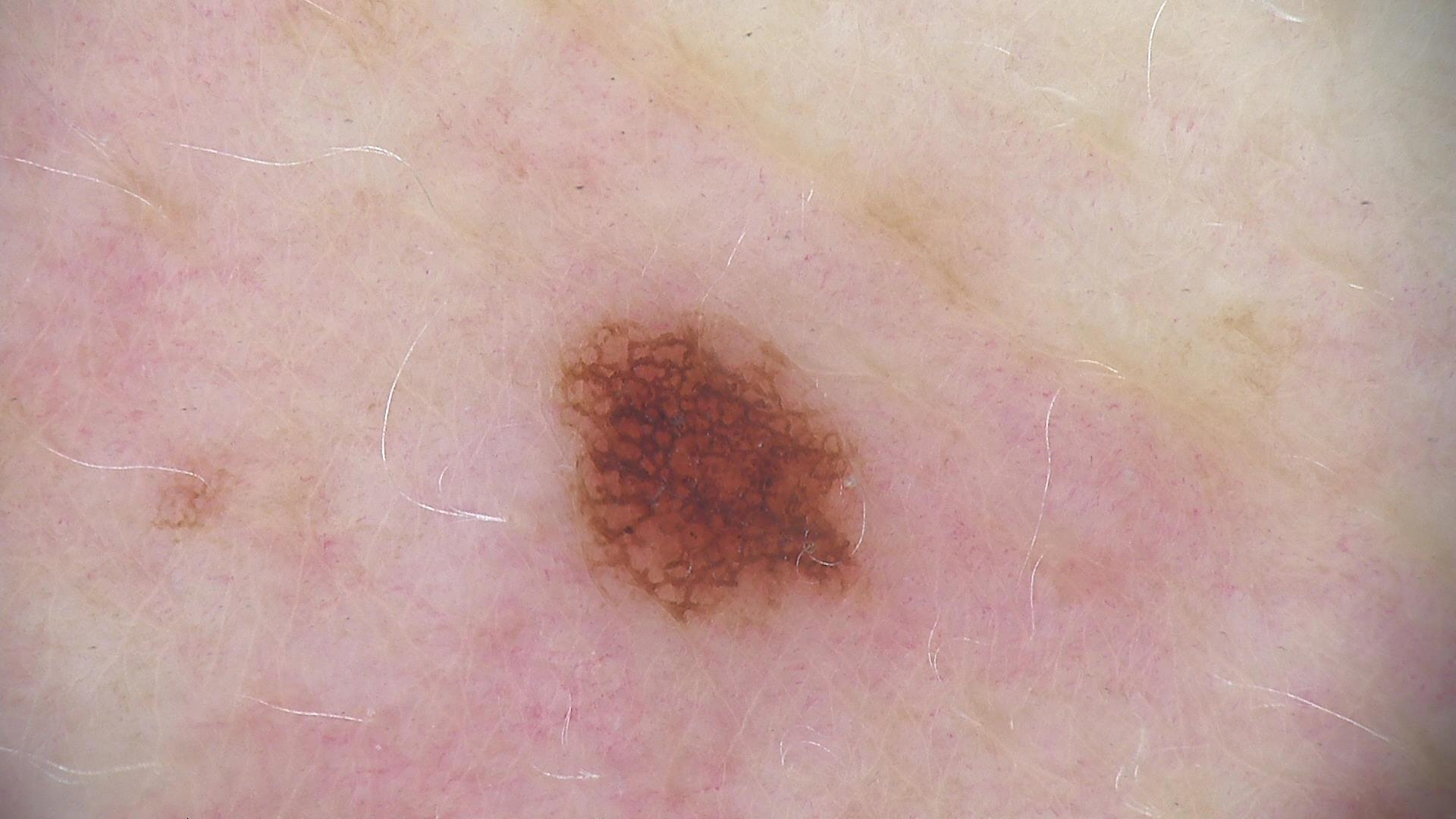| feature | finding |
|---|---|
| image | dermatoscopy |
| diagnosis | dysplastic junctional nevus (expert consensus) |